Dermoscopy of a skin lesion.
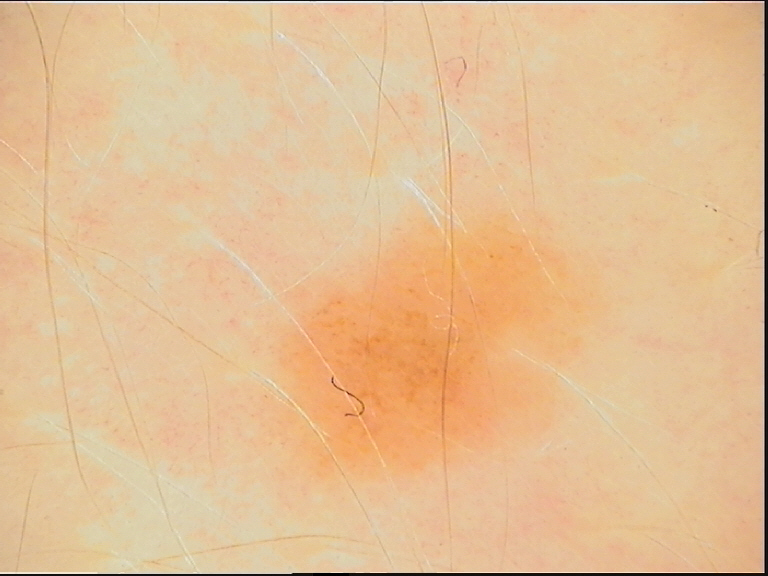category: banal | label: junctional nevus (expert consensus).